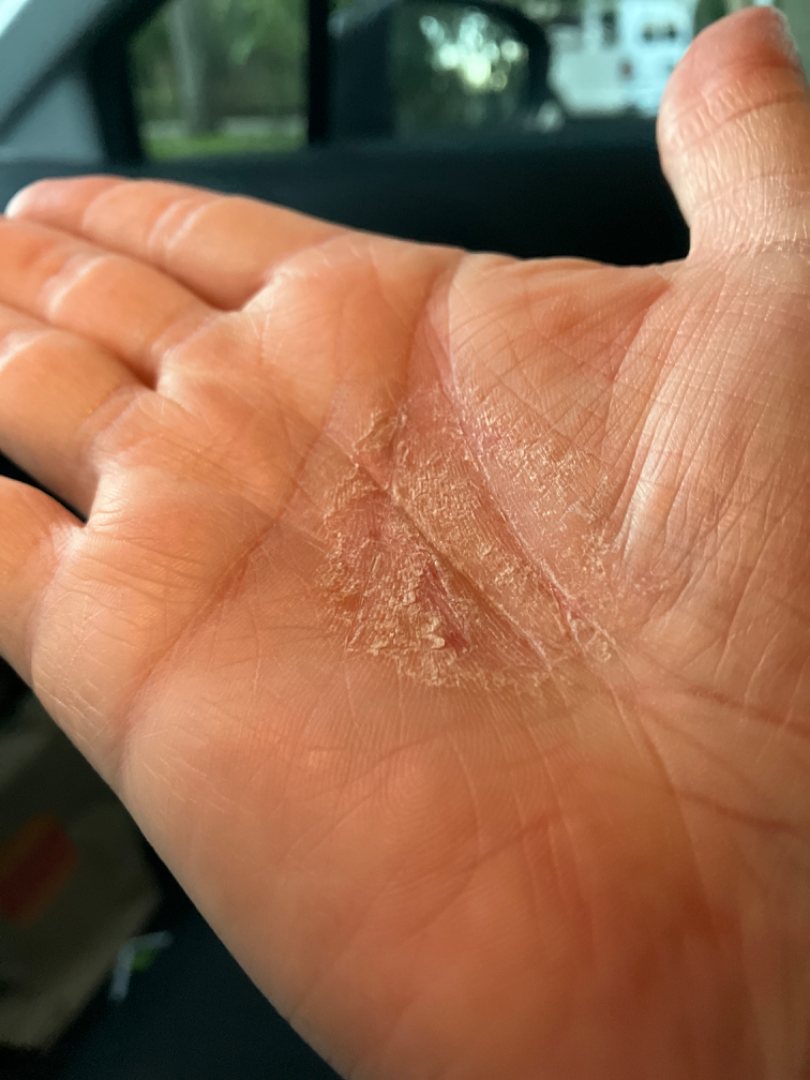The patient described the issue as a rash. The contributor reports the condition has been present for three to twelve months. The photograph was taken at an angle. The lesion is associated with bothersome appearance. On photographic review, the leading consideration is Psoriasis; also raised was Eczema; an alternative is Allergic Contact Dermatitis.